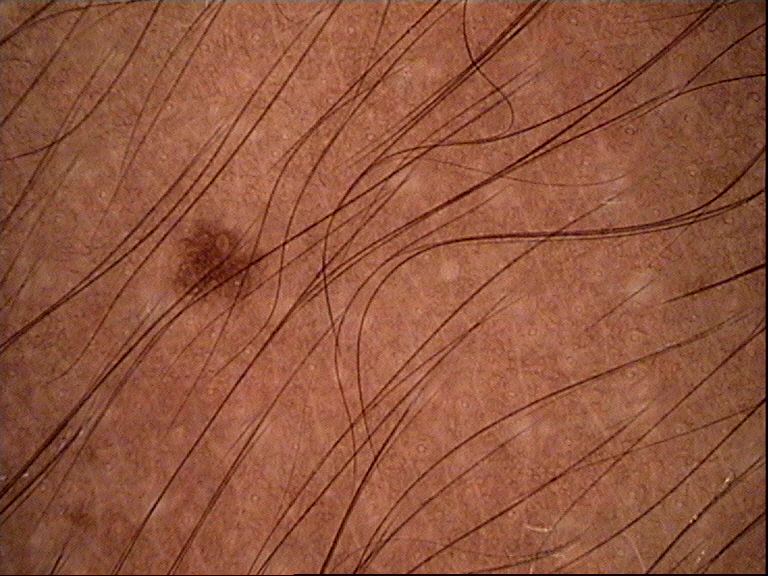A dermoscopic photograph of a skin lesion. This is a banal lesion. Diagnosed as a junctional nevus.